The photograph is a close-up of the affected area · the lesion involves the front of the torso · the subject is 18–29, male: 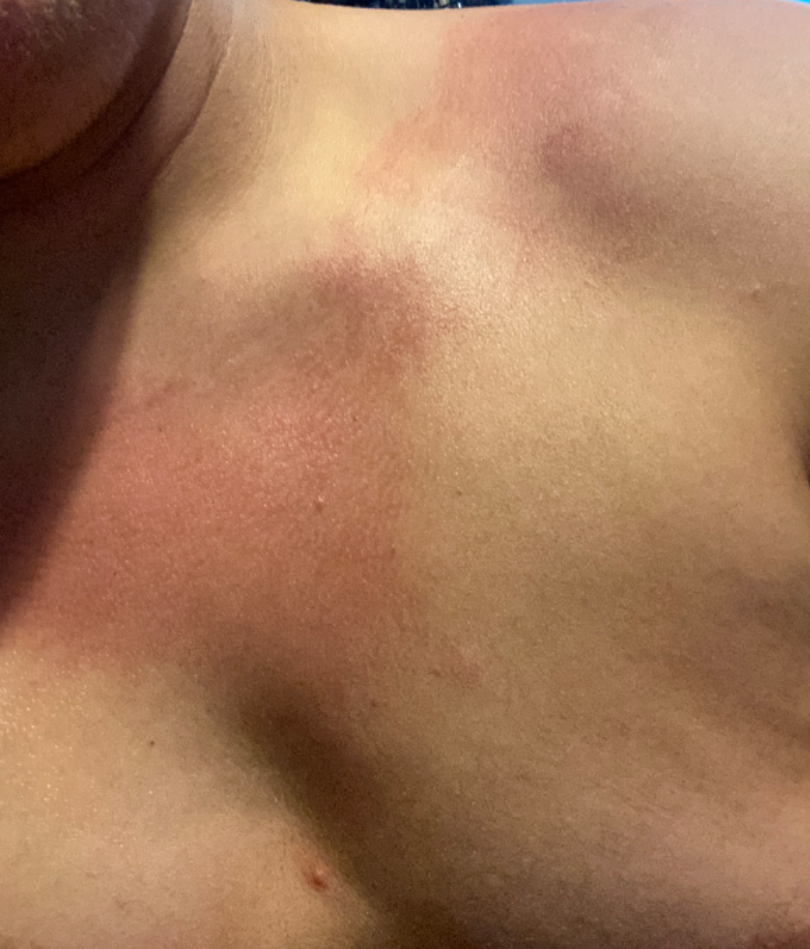Diagnostic features were not clearly distinguishable in this photograph.